A skin lesion imaged with a dermatoscope:
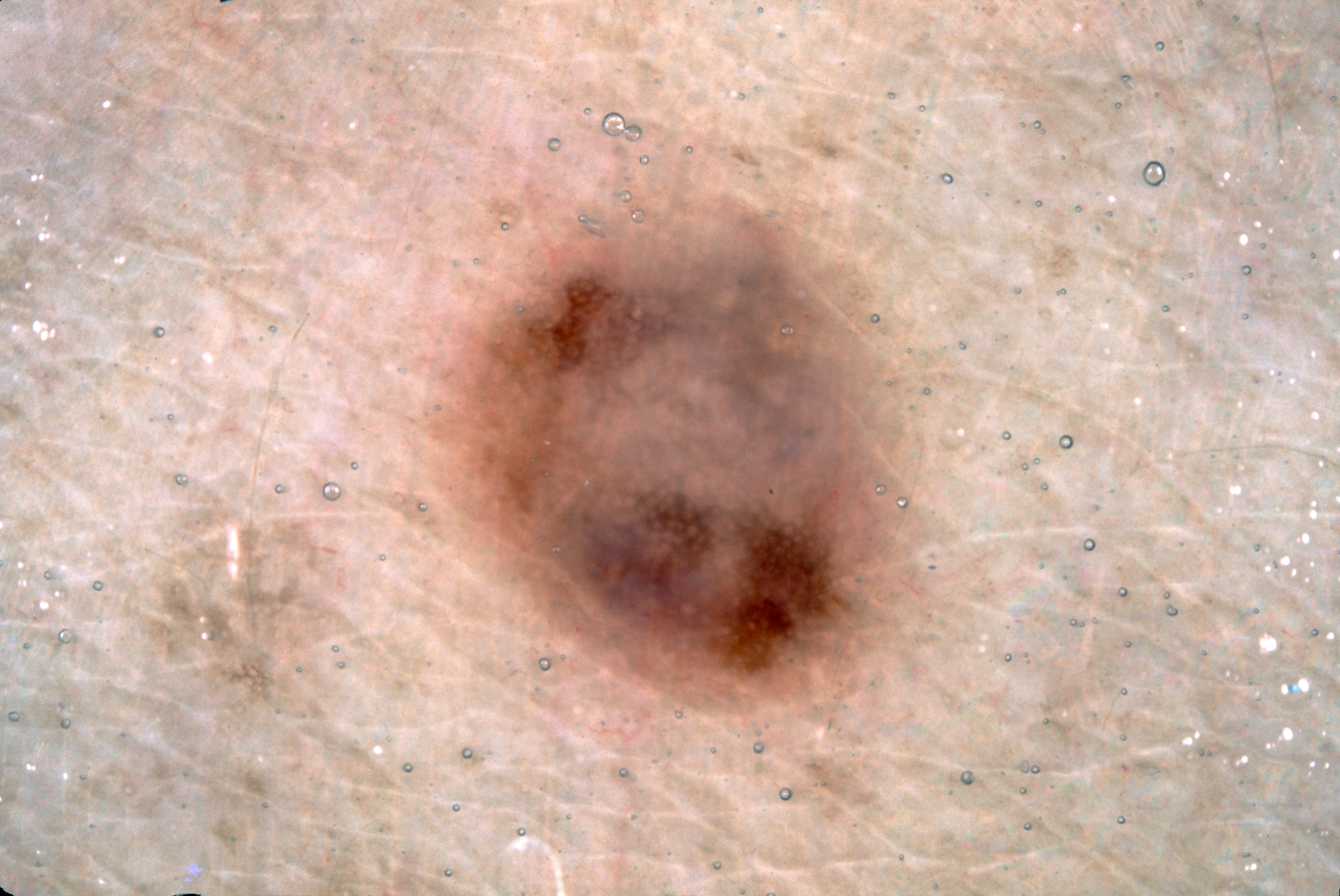Findings:
The visible lesion spans bbox=[405, 145, 959, 753]. Dermoscopy demonstrates pigment network; no negative network, streaks, or milia-like cysts.
Conclusion:
Diagnosed as a melanocytic nevus.